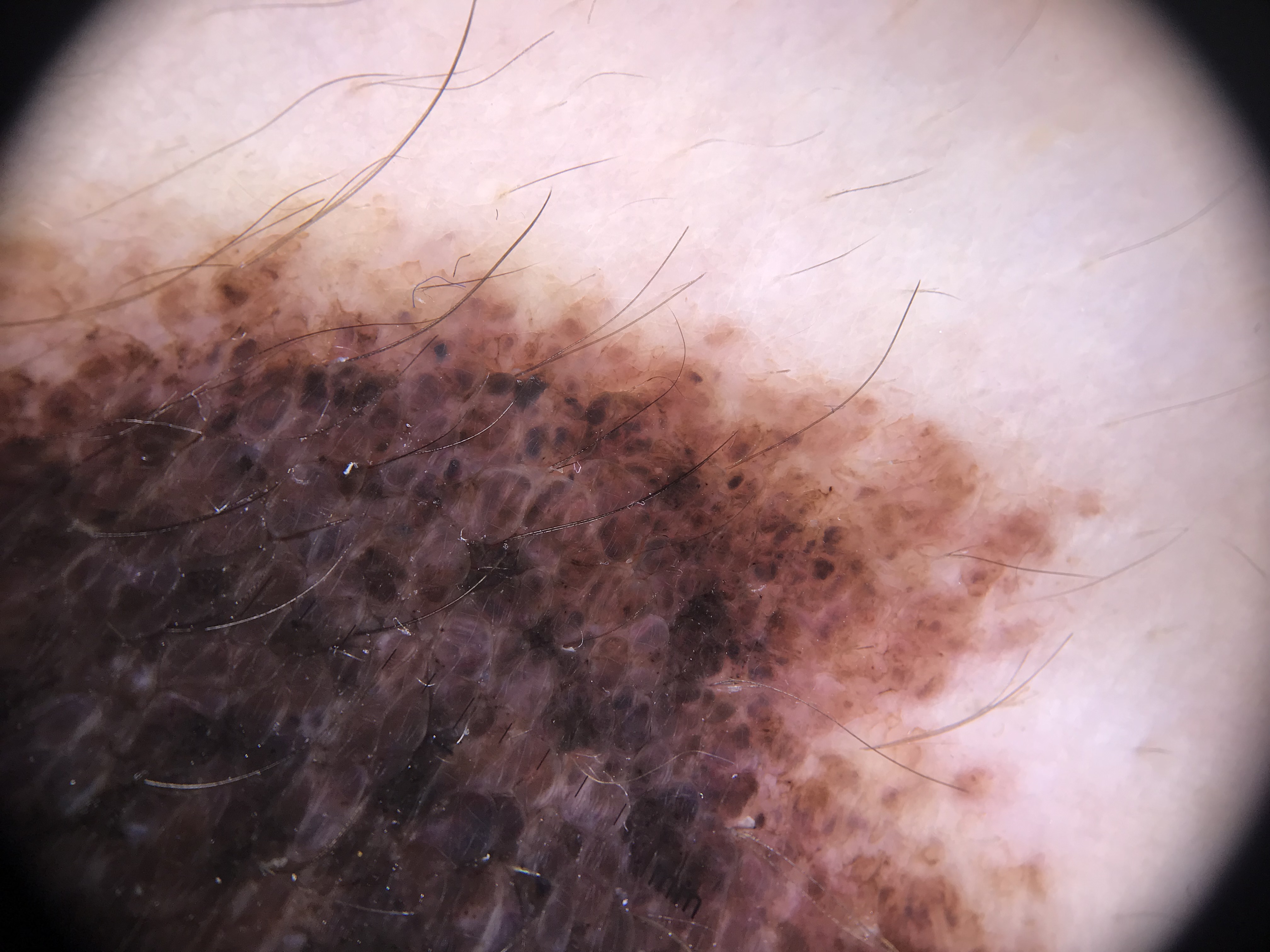modality=dermoscopy
category=banal
diagnostic label=congenital compound nevus (expert consensus)